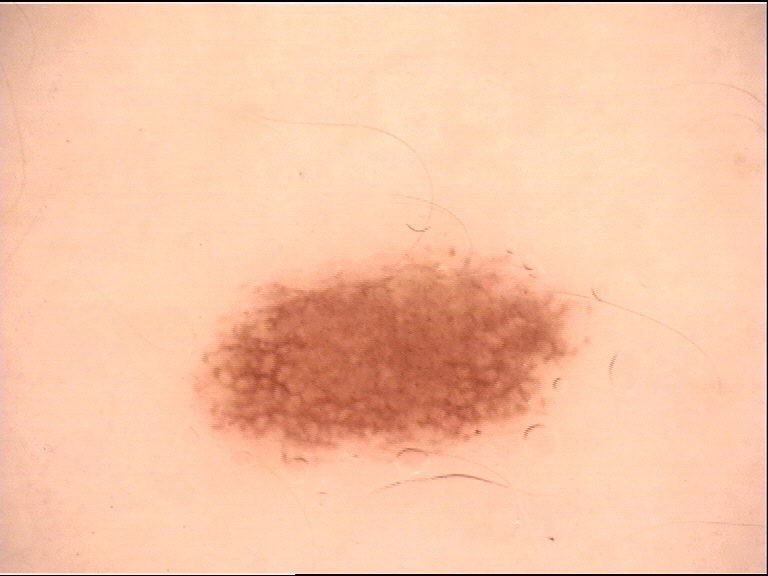Q: What kind of image is this?
A: dermatoscopy
Q: What is the diagnosis?
A: dysplastic junctional nevus (expert consensus)